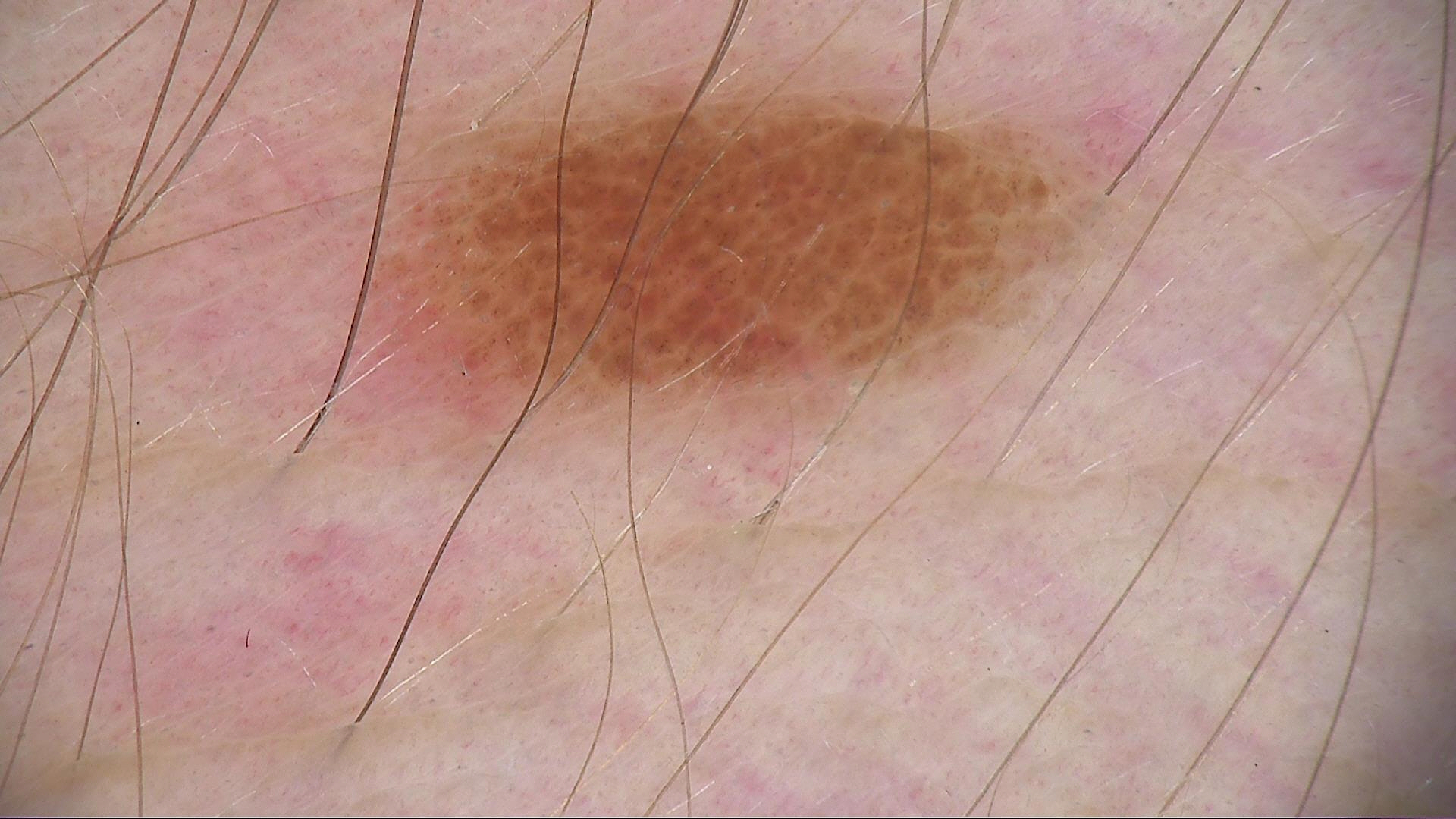Diagnosed as a banal lesion — a compound nevus.